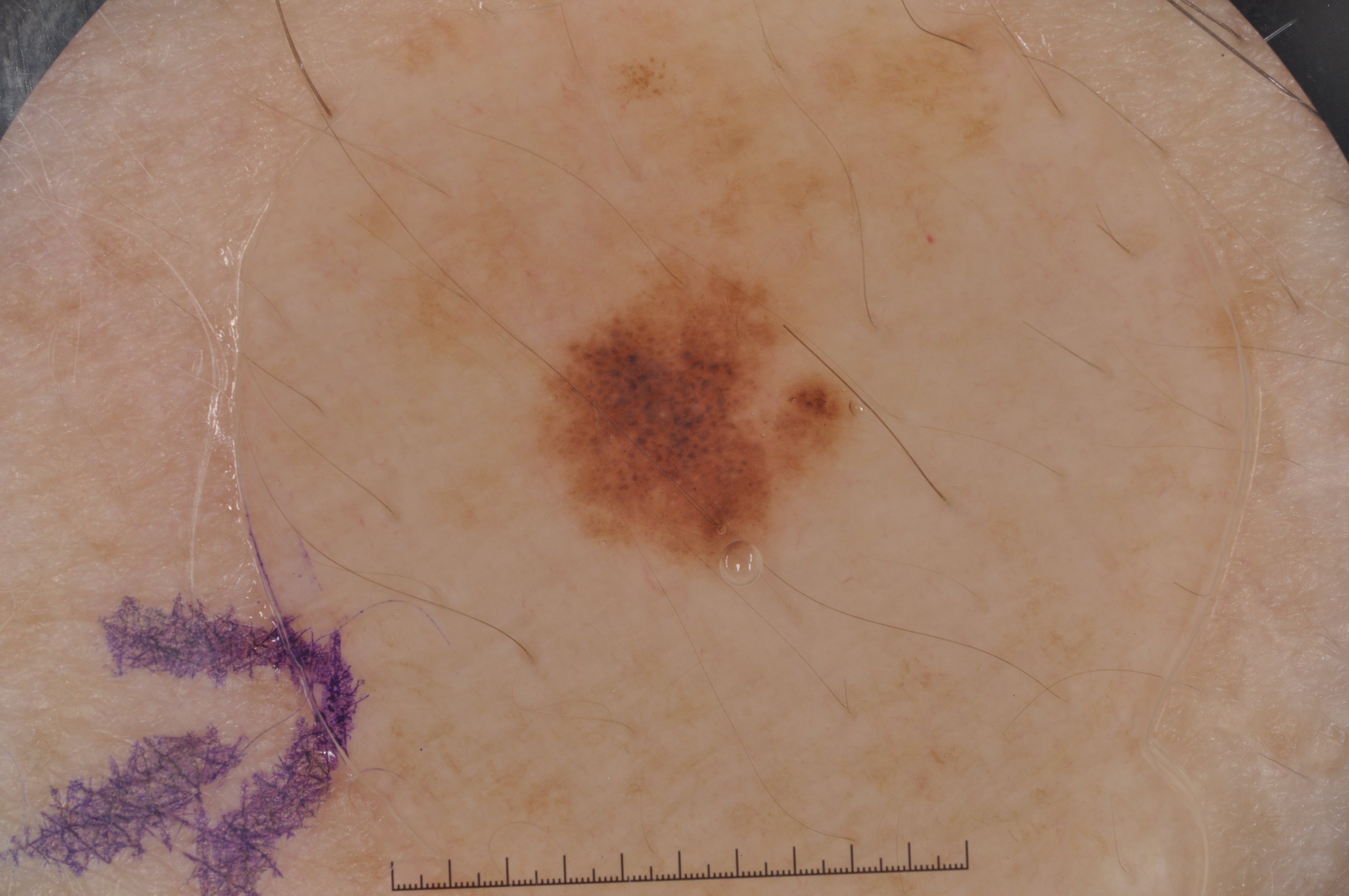A female subject aged around 75.
A dermoscopic close-up of a skin lesion.
Dermoscopically, the lesion shows no negative network, pigment network, milia-like cysts, or streaks.
The lesion covers approximately 6% of the dermoscopic field.
The lesion occupies the region <bbox>538, 266, 854, 567</bbox>.
Histopathological examination showed a melanoma.